A dermatoscopic image of a skin lesion.
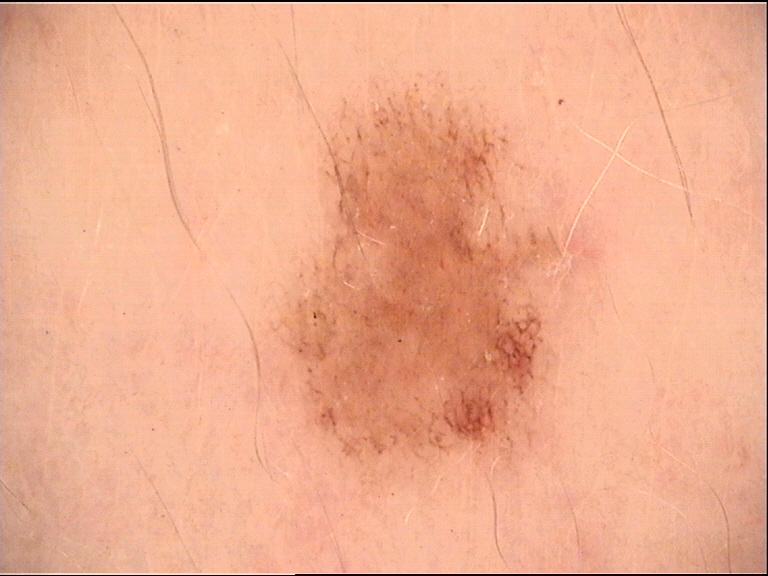Conclusion: Consistent with a benign lesion — a dysplastic junctional nevus.